Located on the top or side of the foot · the patient is male · the patient reported no systemic symptoms · the patient indicates the condition has been present for more than five years · the lesion is associated with itching and bothersome appearance · the photo was captured at a distance · the patient considered this a rash — 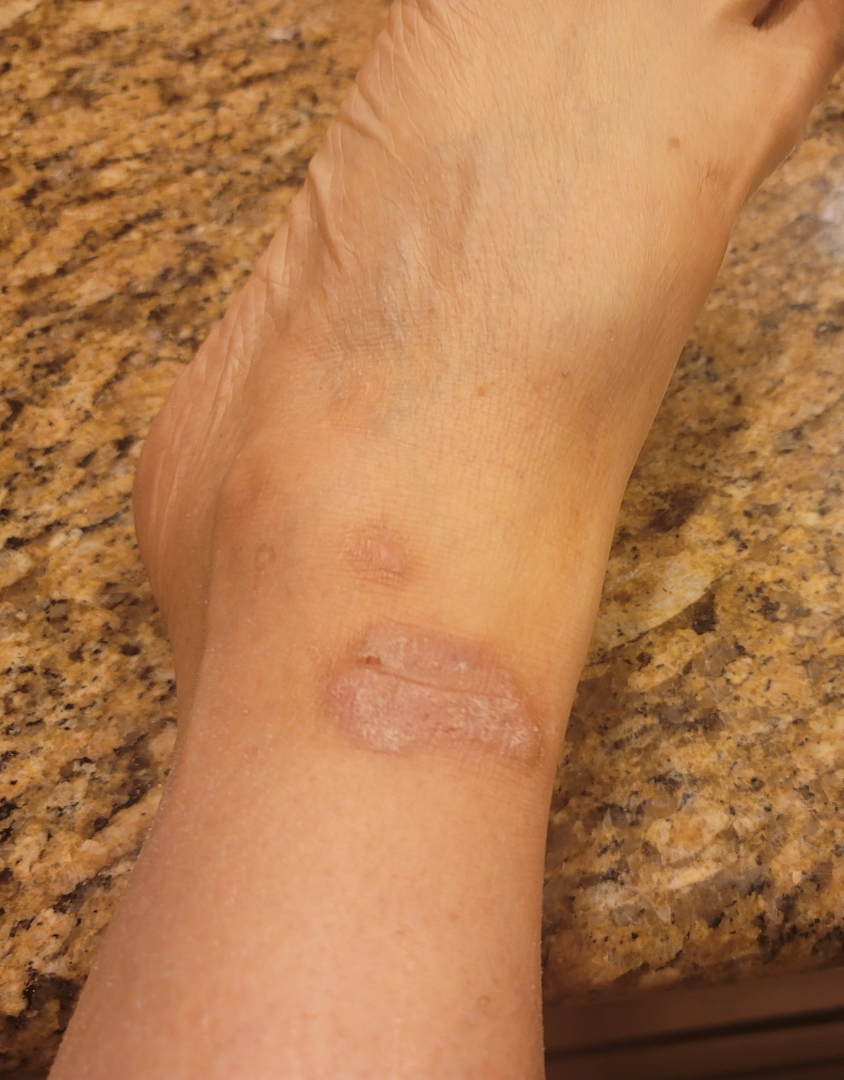Lichen Simplex Chronicus (most likely); Eczema (considered); Psoriasis (unlikely); Pemphigus vulgaris (unlikely).